The photo was captured at a distance. The affected area is the head or neck — 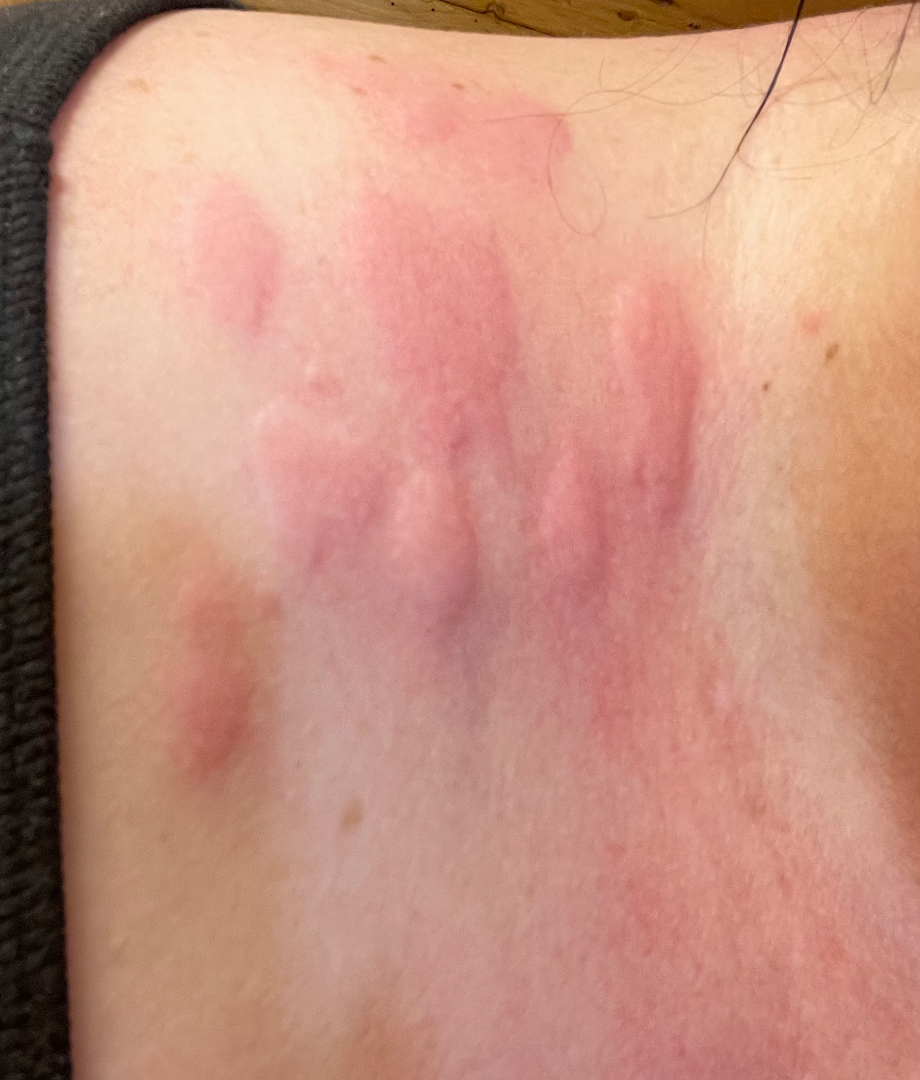Assessment:
On dermatologist assessment of the image: Urticaria (100%).